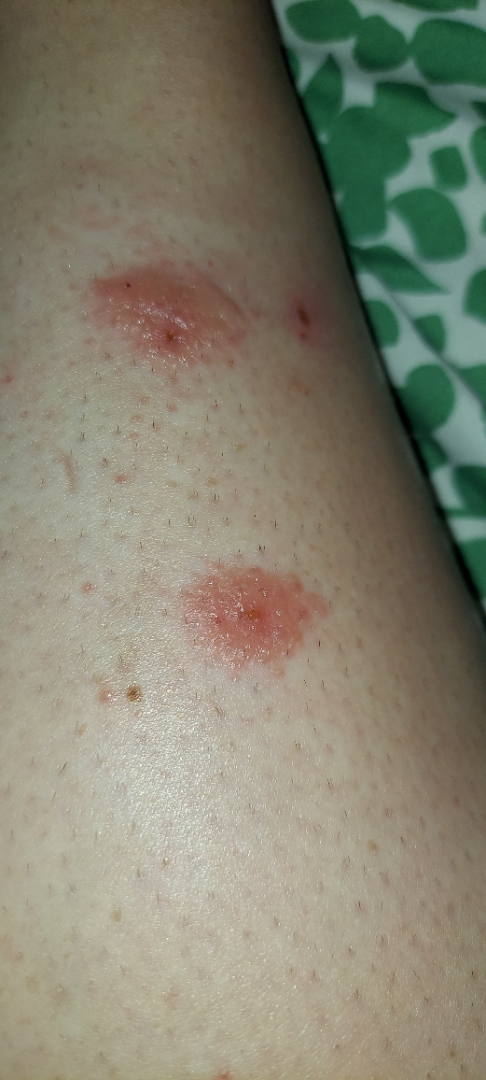subject=female, age 30–39; anatomic site=arm and leg; photo taken=close-up; diagnostic considerations=Eczema and Allergic Contact Dermatitis were each considered, in no particular order.